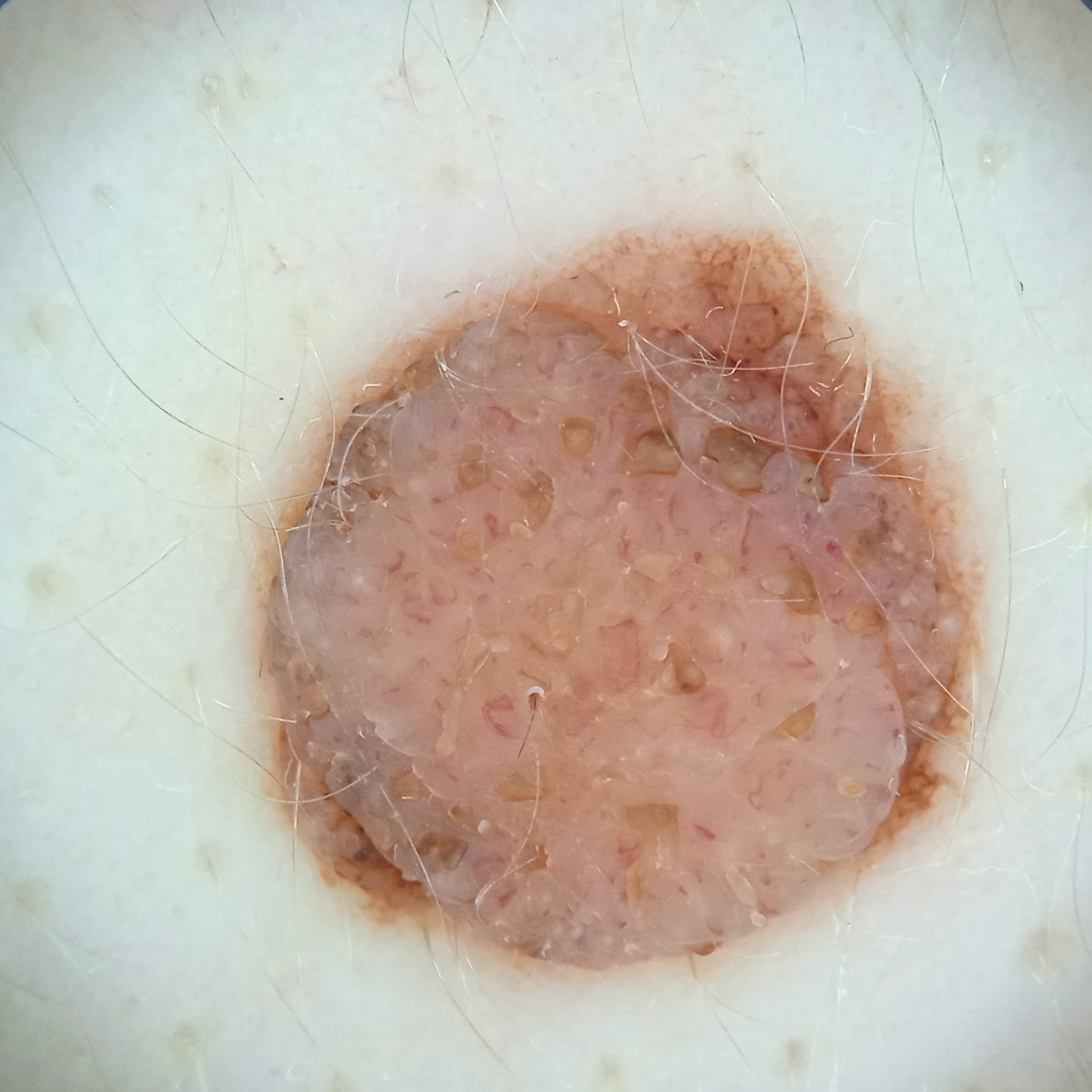Case summary: A female subject aged 26. Acquired for a research image collection, with no referral diagnosis. Dermoscopy of a skin lesion. The lesion is located on the back. The lesion measures approximately 8.9 mm. Conclusion: The consensus diagnosis for this lesion was a melanocytic nevus.